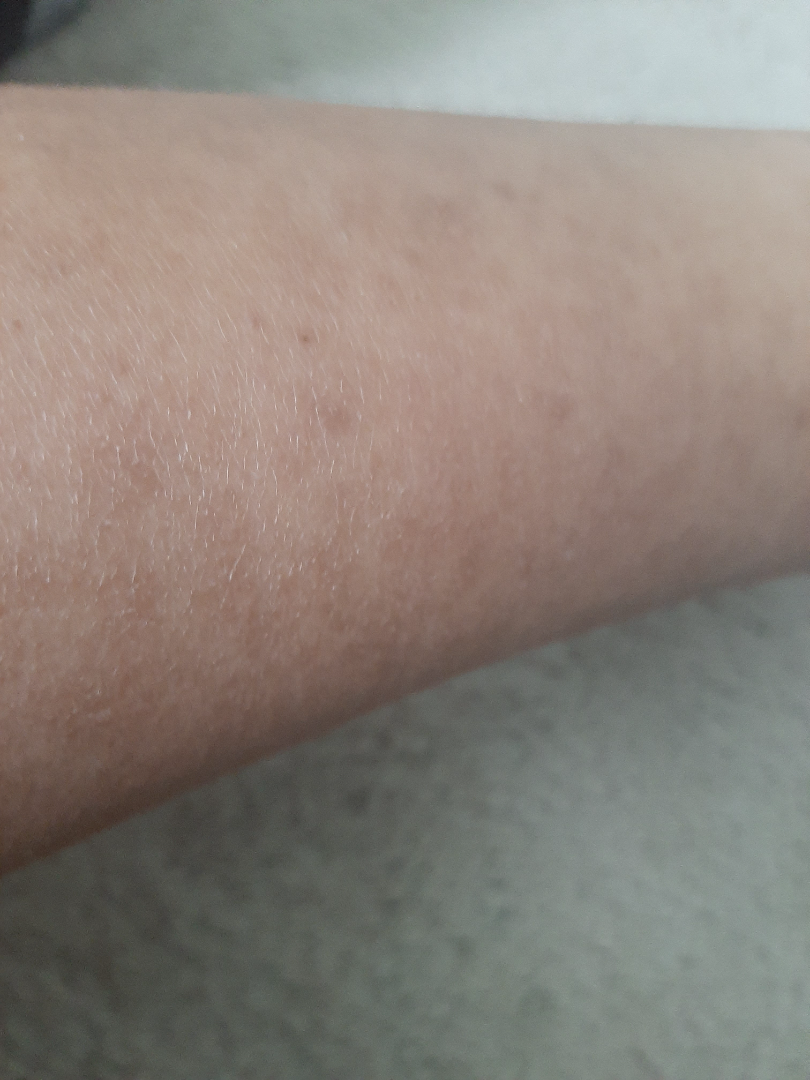The condition could not be reliably identified from the image. The photograph is a close-up of the affected area.